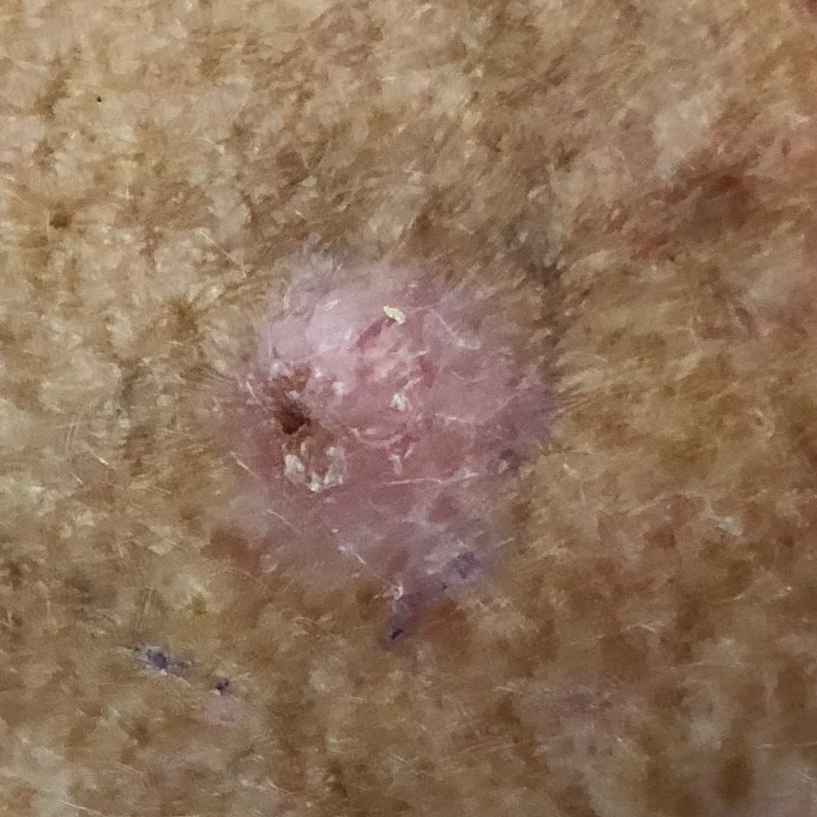Q: Patient demographics?
A: female, in their 50s
Q: What is the imaging modality?
A: clinical photo
Q: What is the patient's skin type?
A: II
Q: What does the exposure history note?
A: prior malignancy (patient or family), alcohol use, prior skin cancer (patient or family), no pesticide exposure
Q: Where on the body is the lesion?
A: the chest
Q: Lesion size?
A: 9x8 mm
Q: Any reported symptoms?
A: itching, bleeding / no pain, no elevation
Q: What did the workup show?
A: basal cell carcinoma (biopsy-proven)